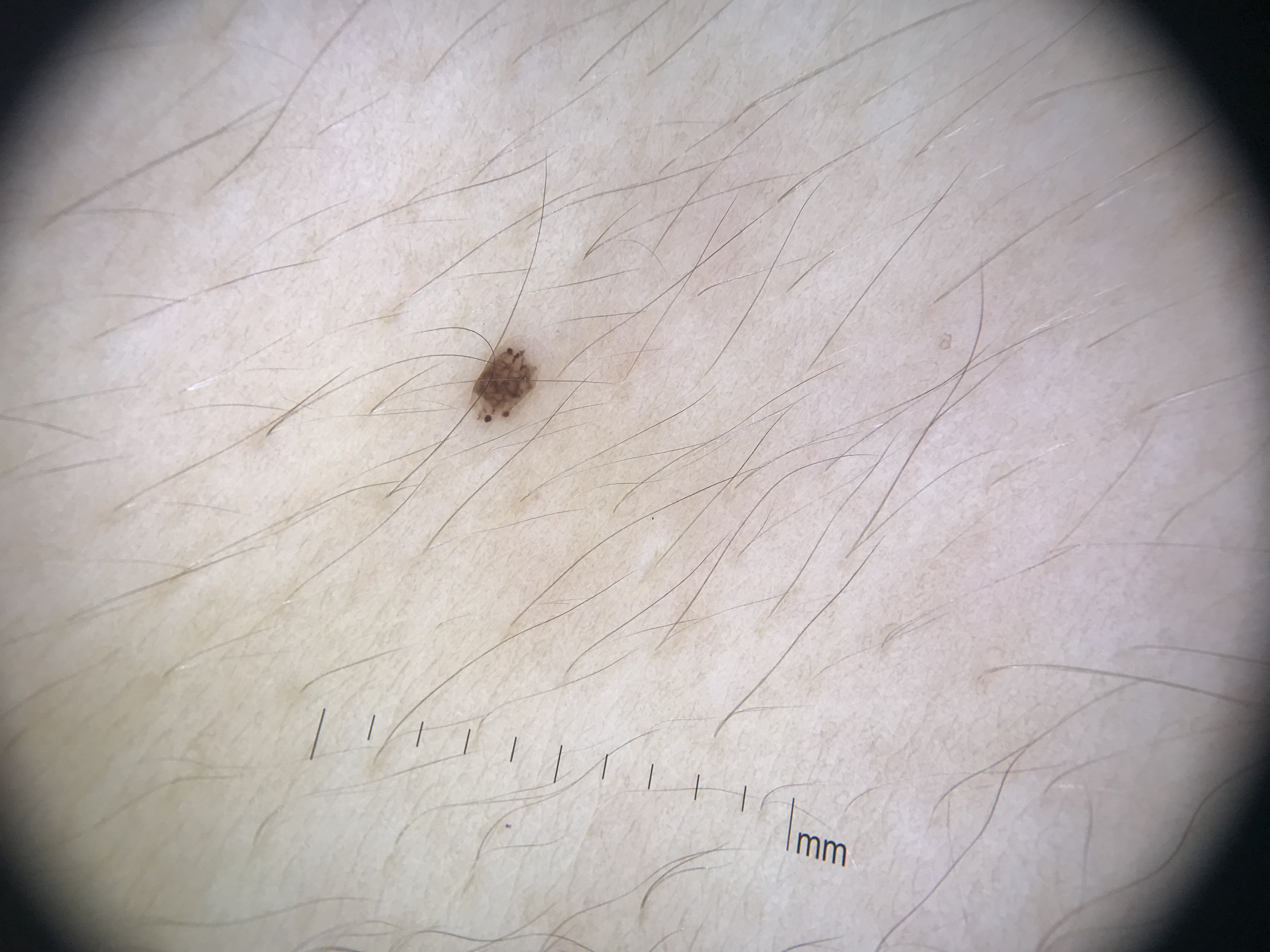{"image": "dermoscopy", "diagnosis": {"name": "dysplastic junctional nevus", "code": "jd", "malignancy": "benign", "super_class": "melanocytic", "confirmation": "expert consensus"}}